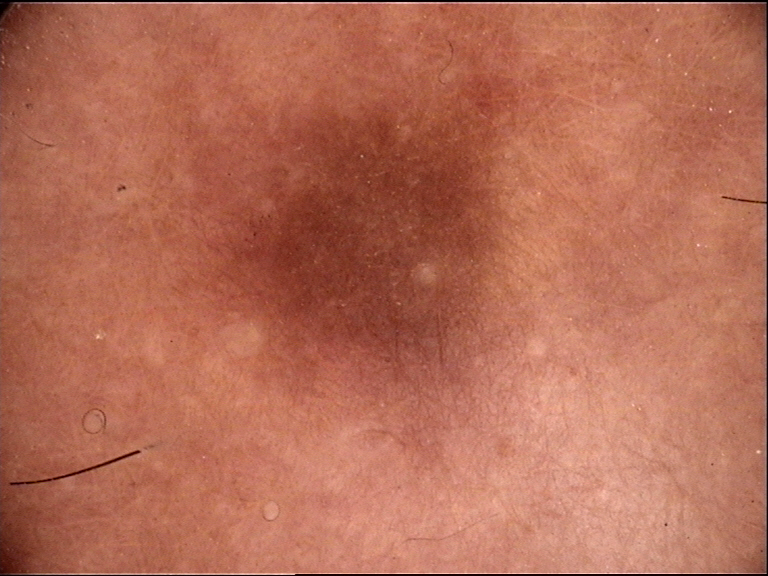<case>
<image>dermoscopy</image>
<diagnosis>
<name>dermatofibroma</name>
<code>df</code>
<malignancy>benign</malignancy>
<super_class>non-melanocytic</super_class>
<confirmation>expert consensus</confirmation>
</diagnosis>
</case>